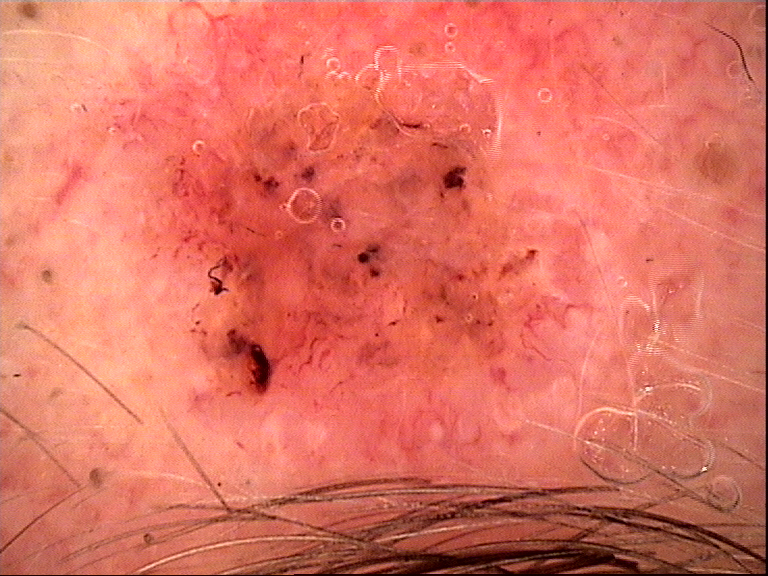Findings: A dermatoscopic image of a skin lesion. The morphology is that of a keratinocytic lesion. Conclusion: Histopathology confirmed a malignancy — a squamous cell carcinoma.